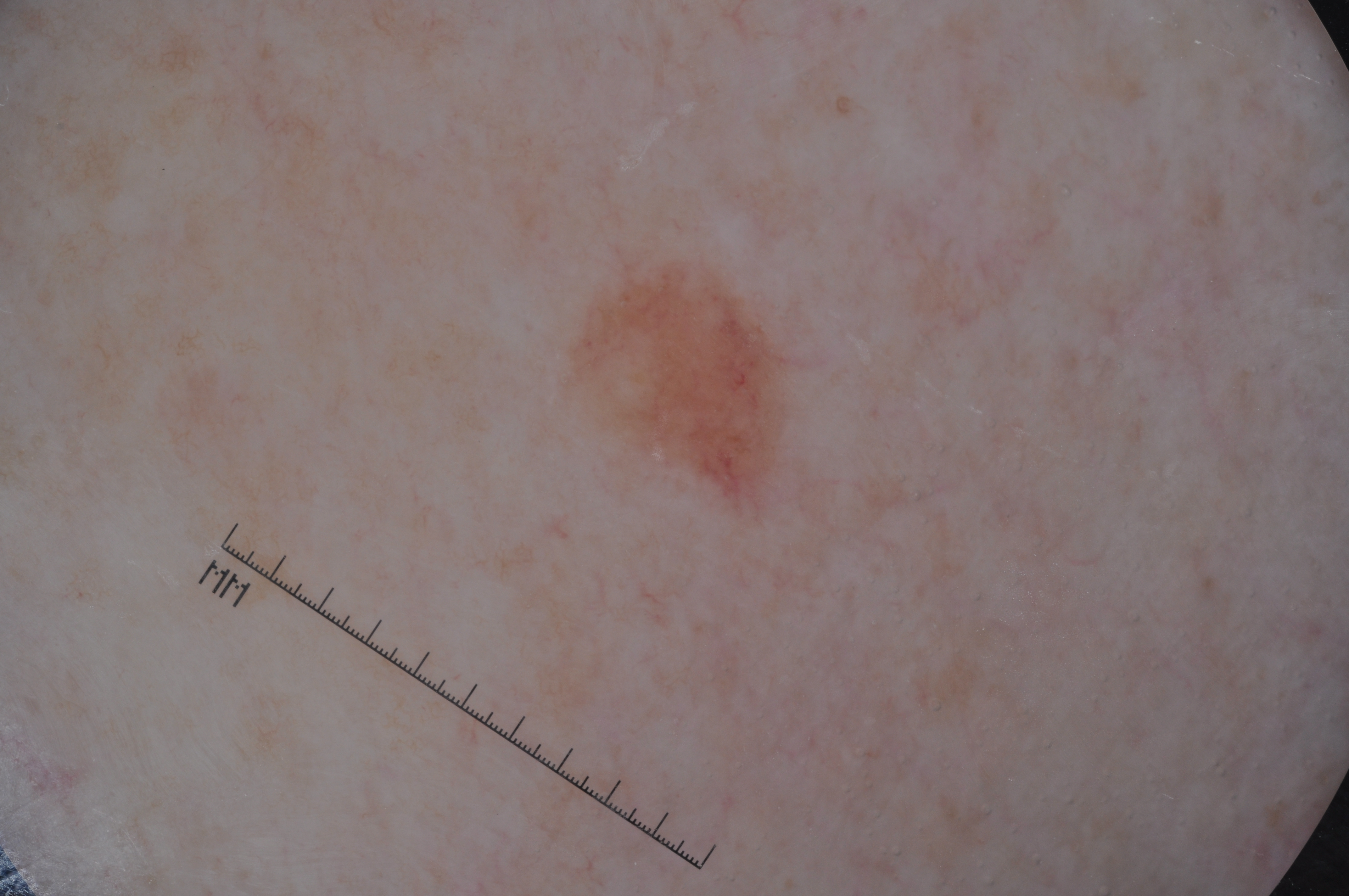<dermoscopy>
  <image>
    <modality>dermoscopy</modality>
  </image>
  <dermoscopic_features>
    <present/>
    <absent>streaks, pigment network, milia-like cysts, negative network</absent>
  </dermoscopic_features>
  <lesion_location>
    <bbox_xyxy>580, 273, 780, 476</bbox_xyxy>
  </lesion_location>
  <diagnosis>
    <name>melanocytic nevus</name>
    <malignancy>benign</malignancy>
    <lineage>melanocytic</lineage>
    <provenance>clinical</provenance>
  </diagnosis>
</dermoscopy>